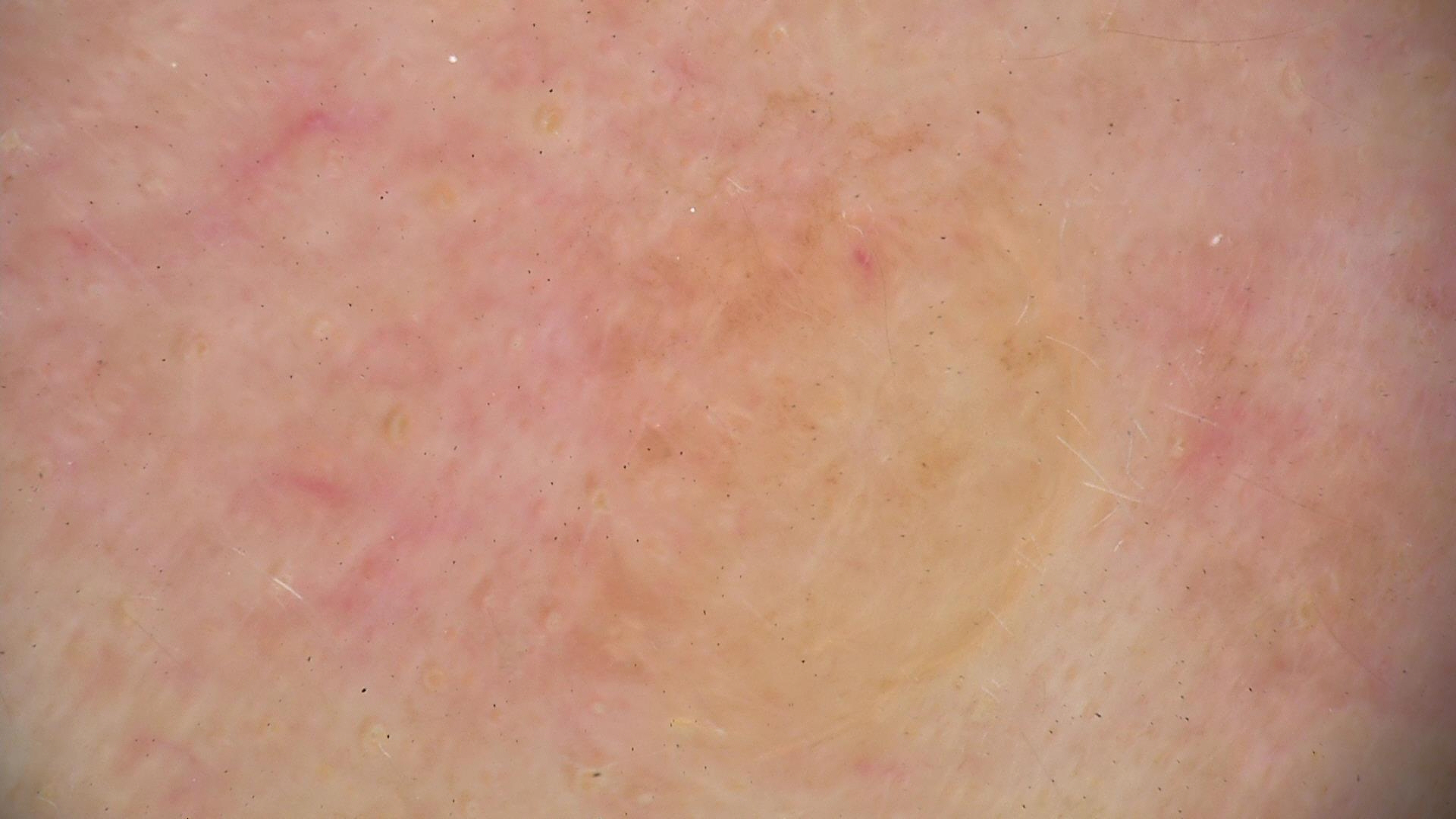Consistent with a banal lesion — a dermal nevus.